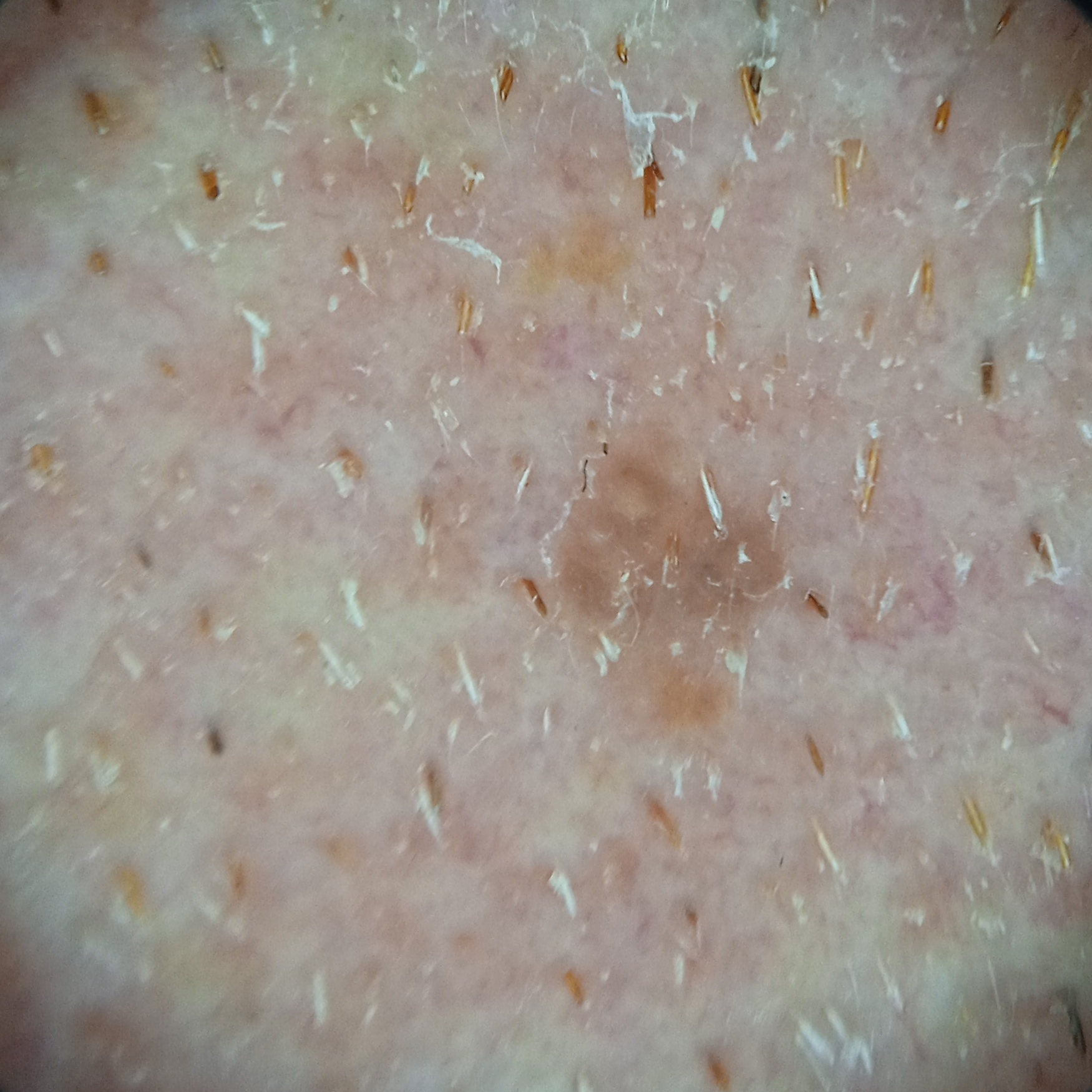Findings:
- diagnostic label: seborrheic keratosis (dermatologist consensus)